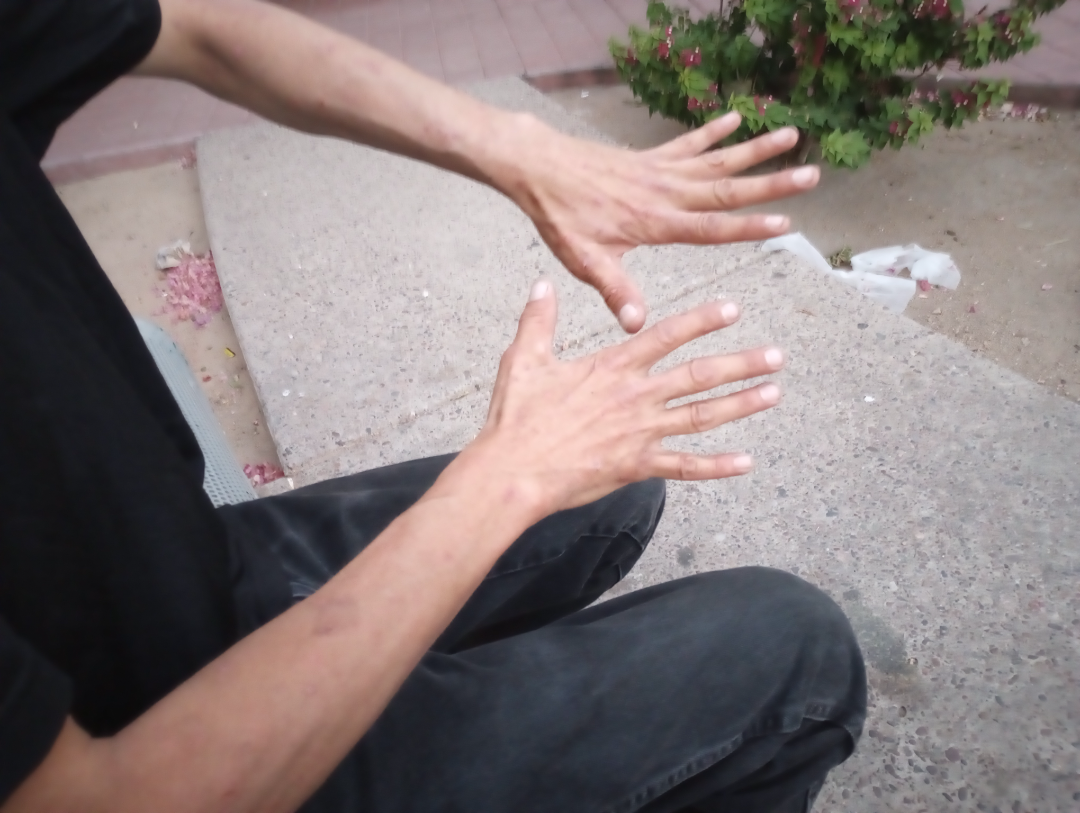Findings:
• assessment · indeterminate from the photograph